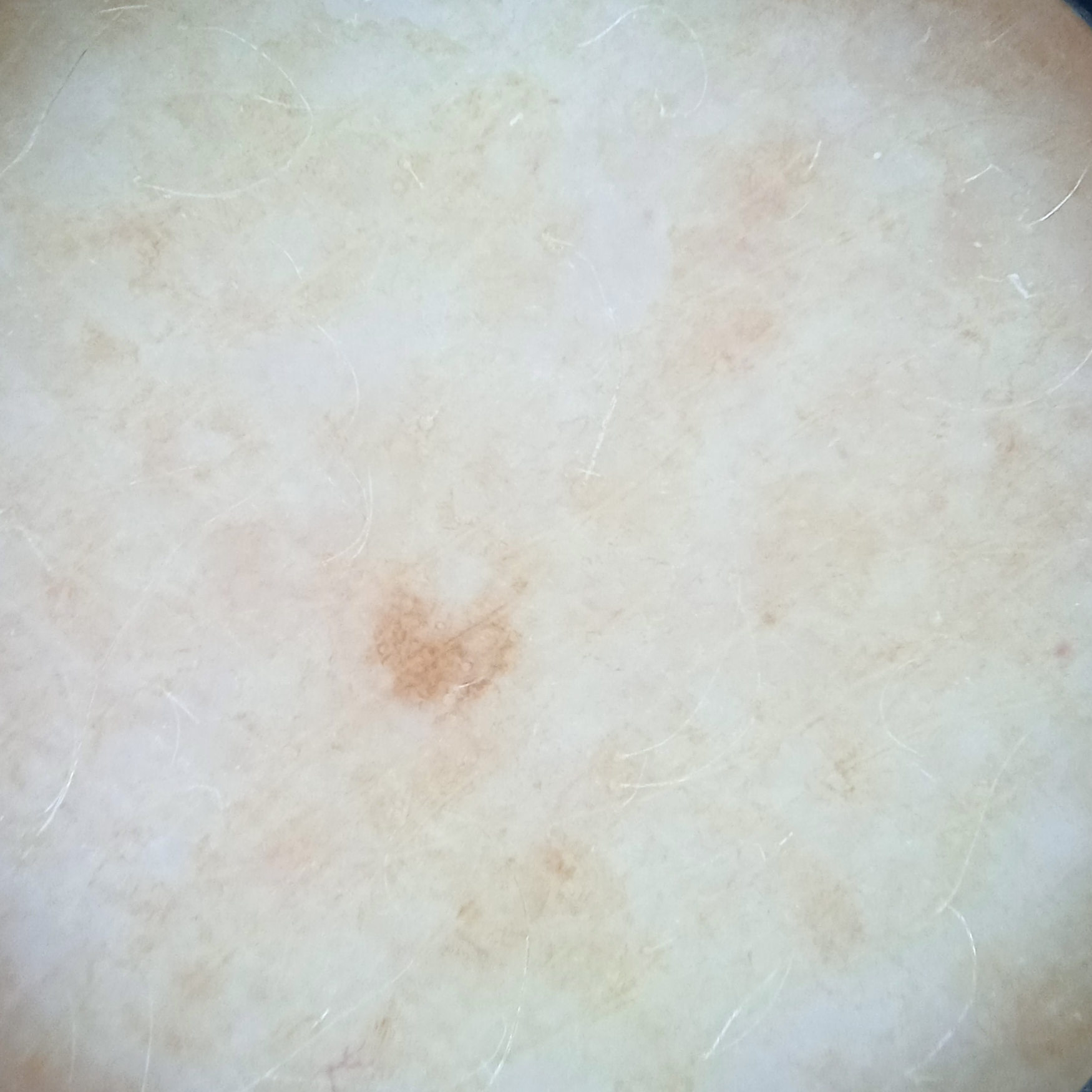* diagnostic label · melanocytic nevus (dermatologist consensus)